The leg is involved; this is a close-up image:
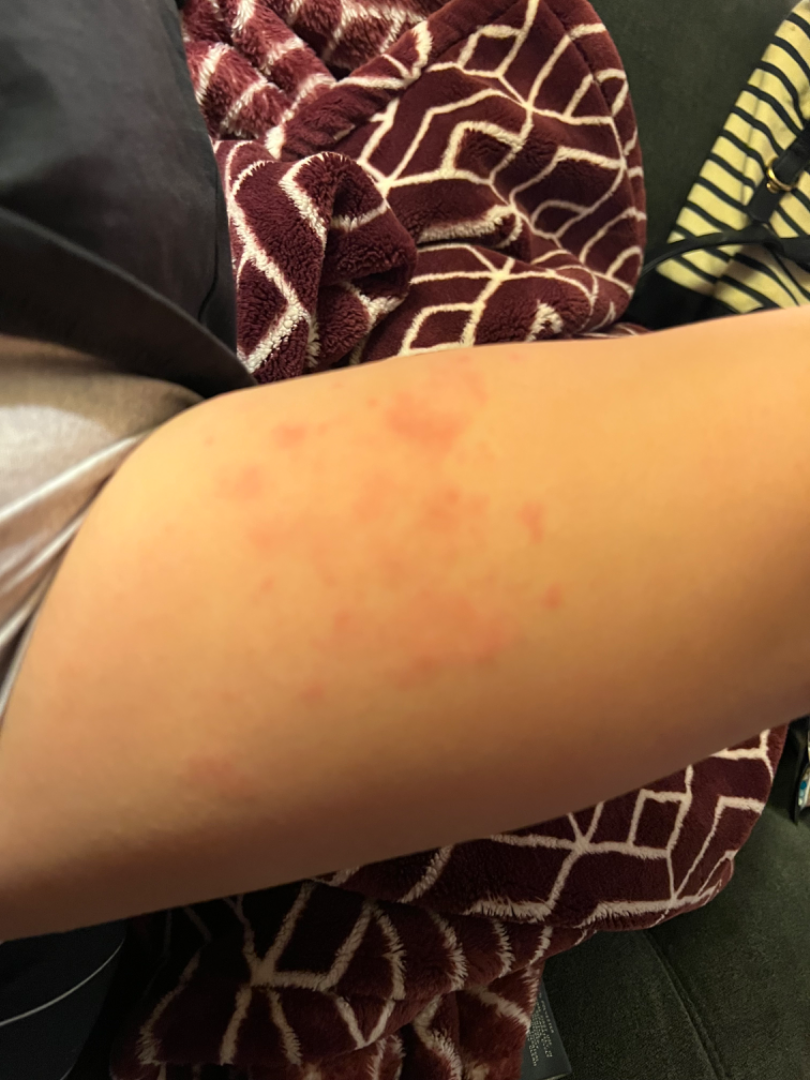Q: Patient's own categorization?
A: a rash
Q: How does the lesion feel?
A: raised or bumpy
Q: What is the dermatologist's impression?
A: Urticaria (67%); Eczema (33%)